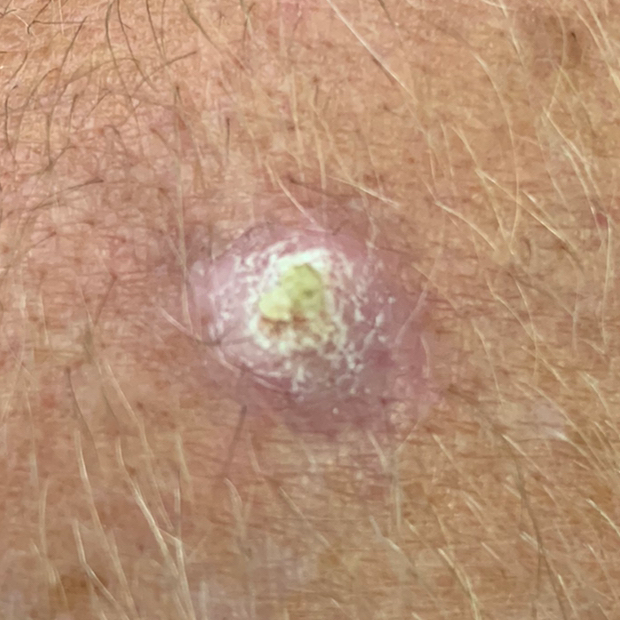A male patient in their early 50s.
Fitzpatrick phototype II.
The lesion involves a forearm.
Measuring about 10 × 10 mm.
By the patient's account, the lesion itches and is elevated.
Biopsy-confirmed as a premalignant lesion — an actinic keratosis.